A skin lesion imaged with a dermatoscope.
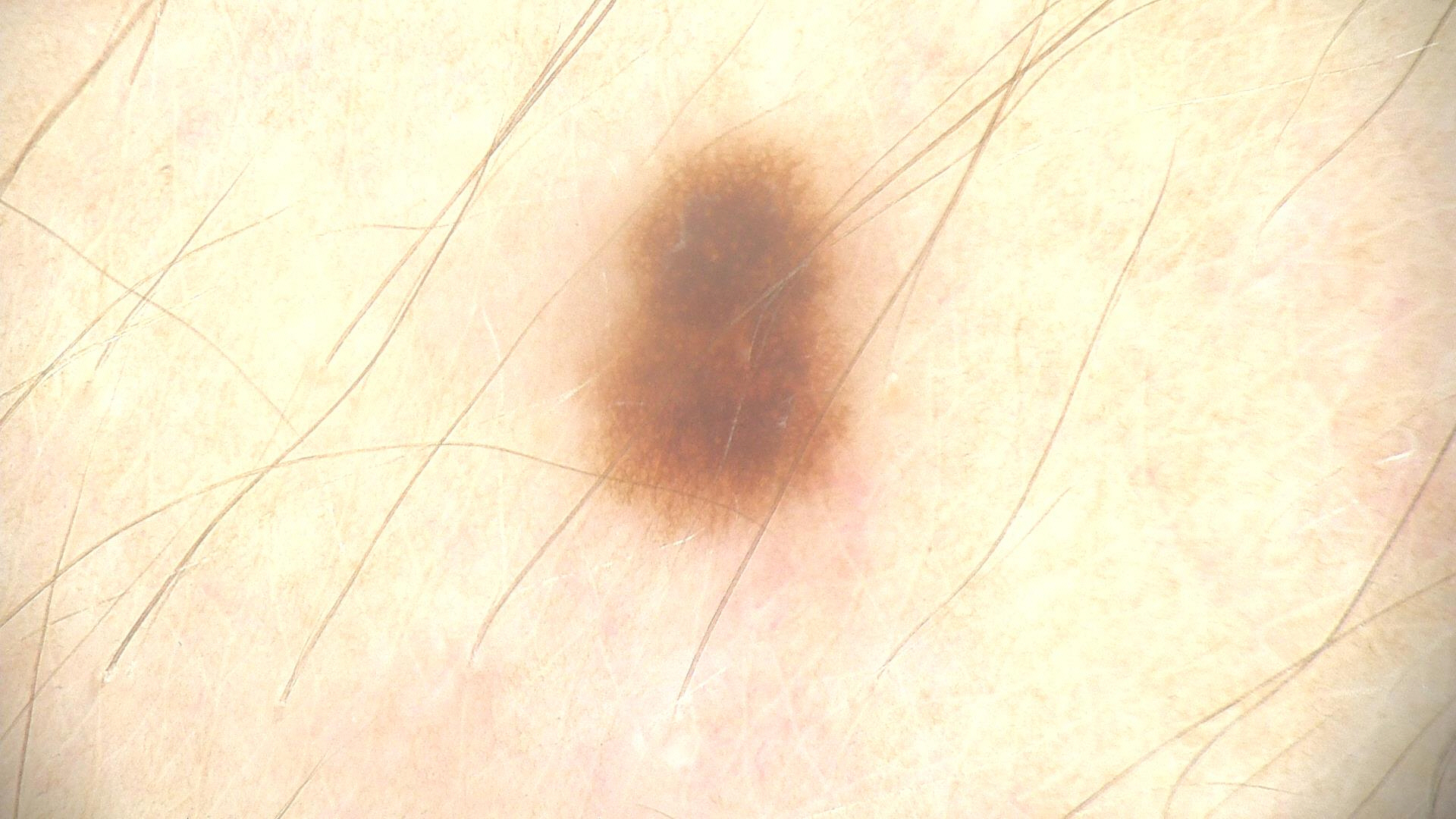Consistent with a benign lesion — a dysplastic junctional nevus.